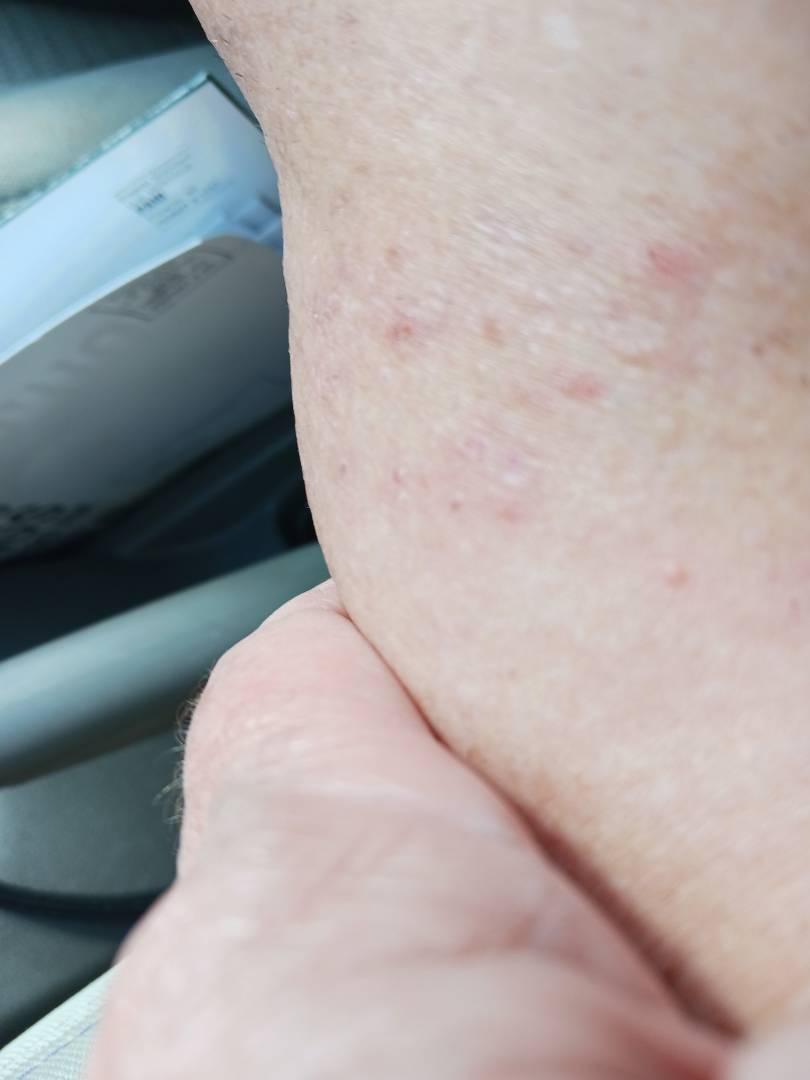Consistent with Eczema.